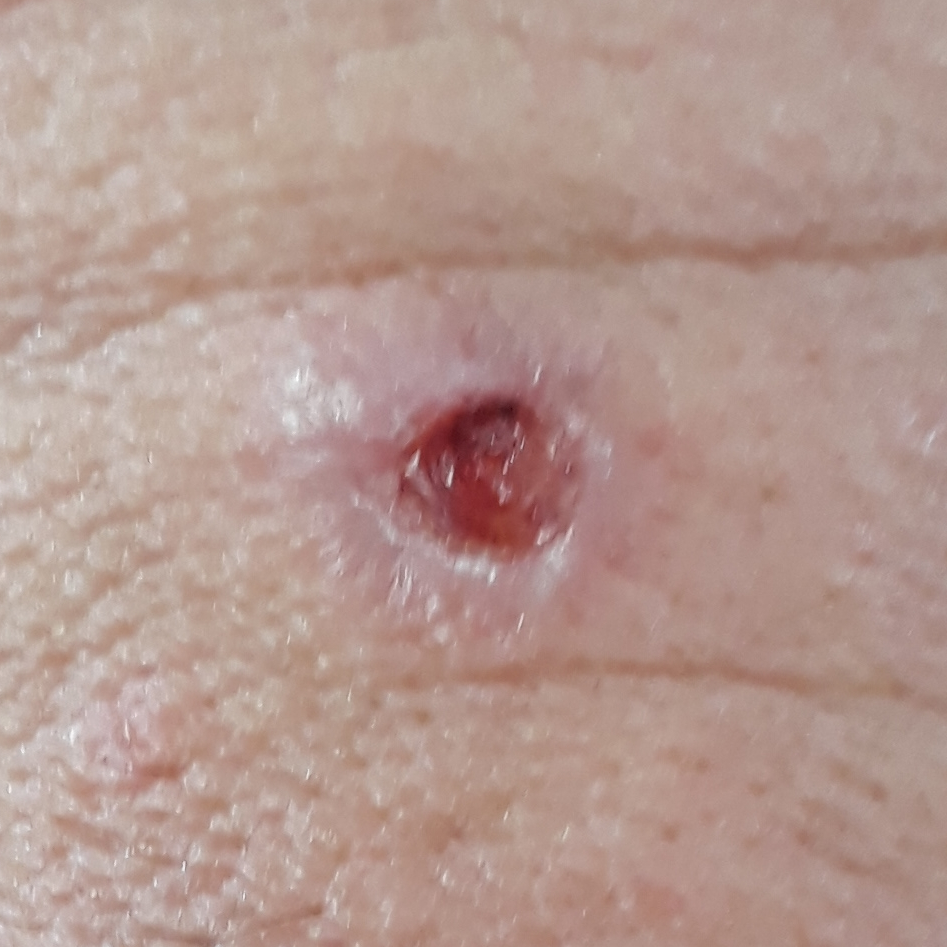Fitzpatrick phototype III. A clinical photograph of a skin lesion. A male patient 61 years old. The patient describes that the lesion is elevated, has bled, itches, and hurts. The biopsy diagnosis was a basal cell carcinoma.